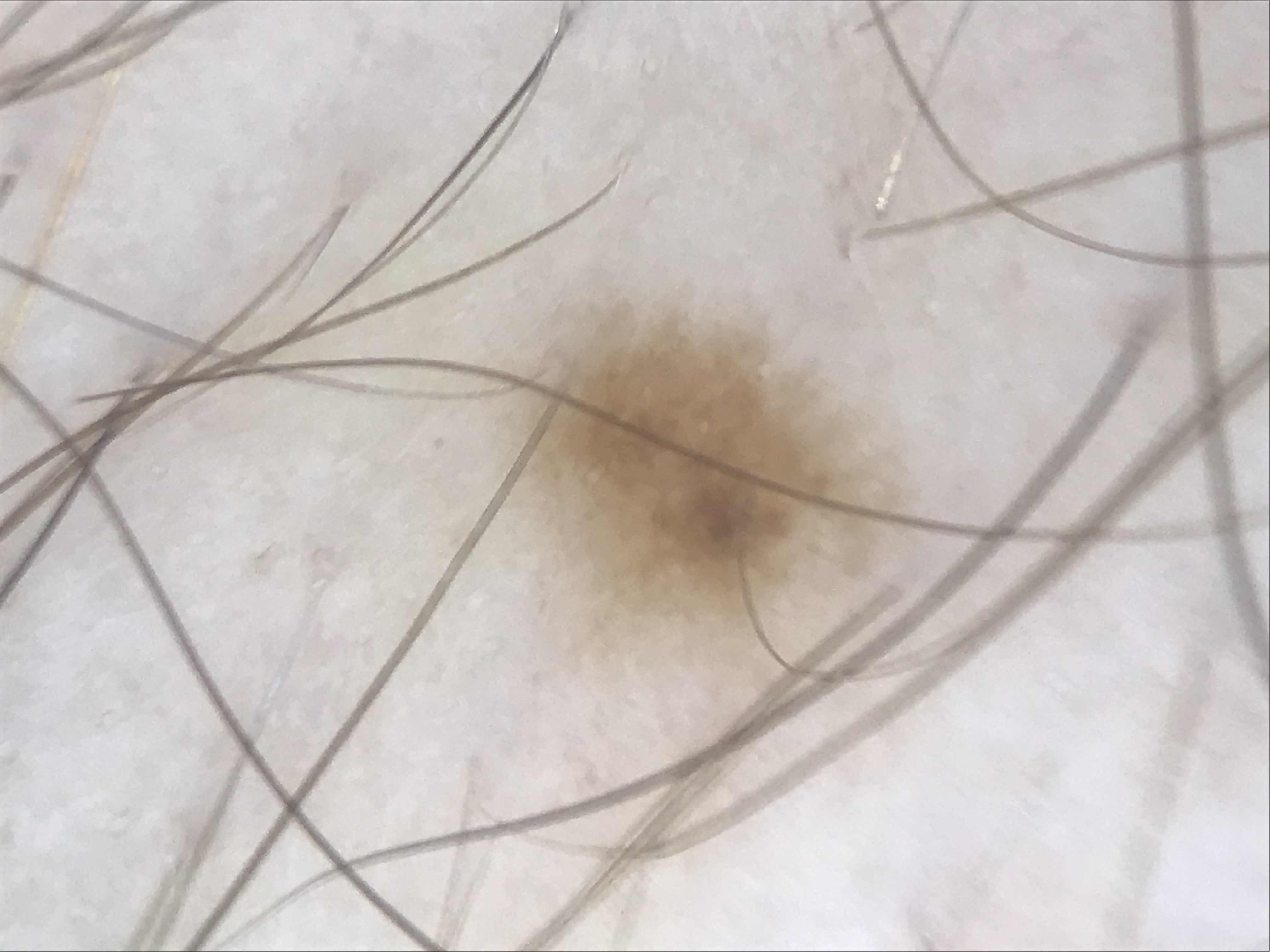The architecture is that of a banal lesion.
The diagnostic label was a junctional nevus.